Dermoscopy of a skin lesion:
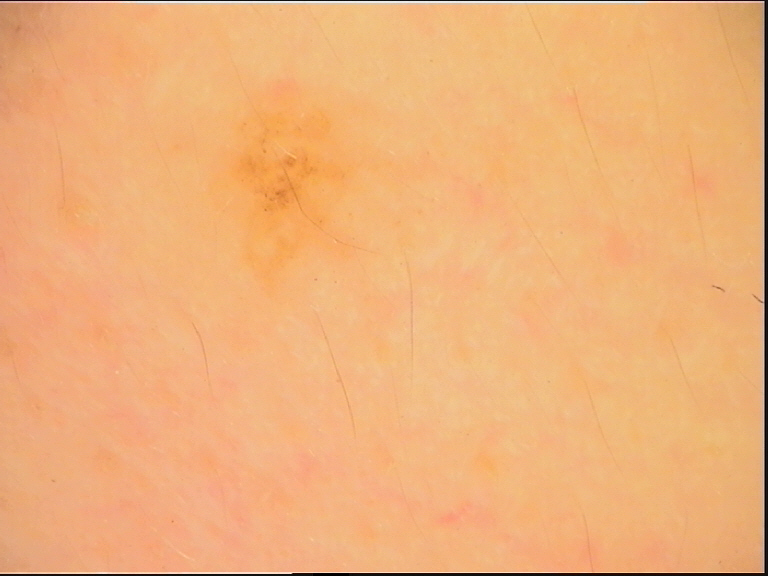Q: How is the lesion classified?
A: banal
Q: What is this lesion?
A: dermal nevus (expert consensus)